Located on the arm. Present for one to three months. The lesion is described as raised or bumpy. The photo was captured at a distance. The subject is 18–29, male. Self-categorized by the patient as a rash. The patient reports bothersome appearance and enlargement. No relevant systemic symptoms — 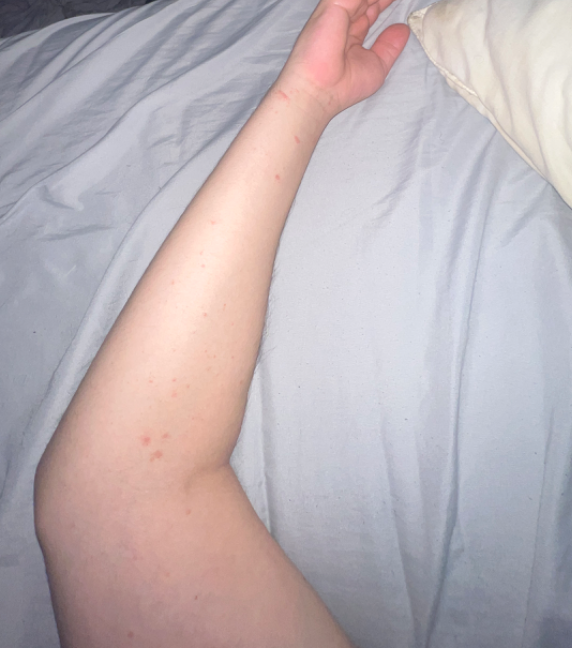On teledermatology review: the favored diagnosis is Allergic Contact Dermatitis.